This image was taken at a distance: 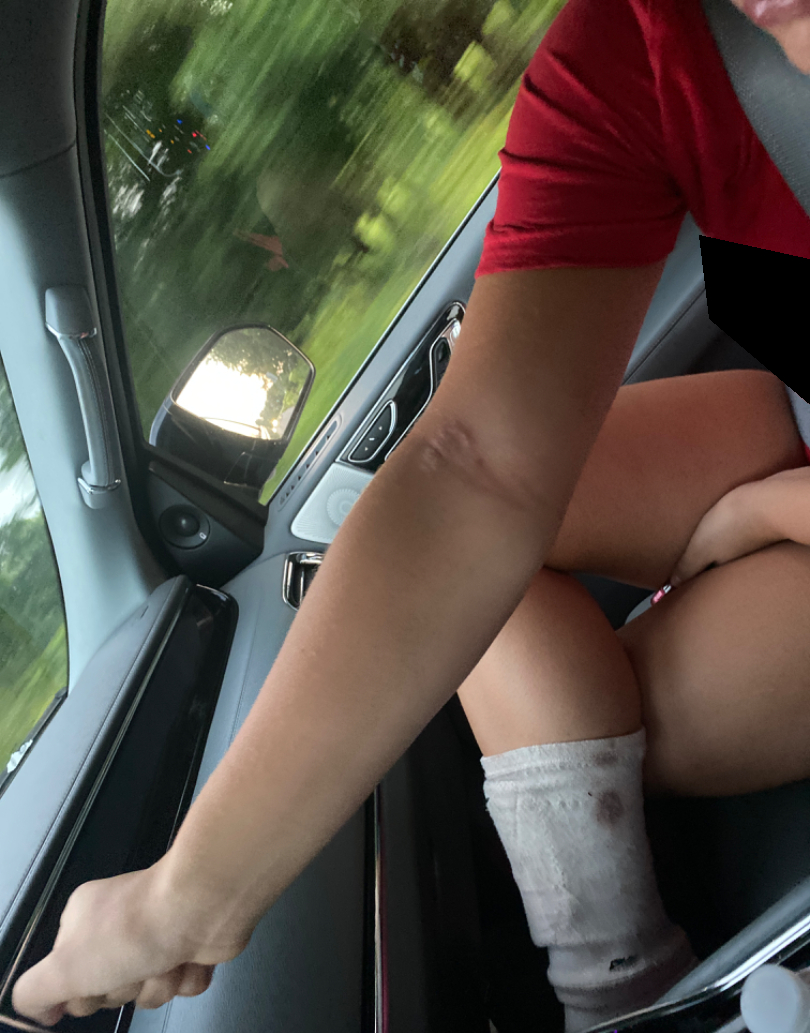On photographic review by a dermatologist: Eczema (most likely).